Located on the leg, arm and front of the torso; the photo was captured at a distance; male contributor, age 18–29 — 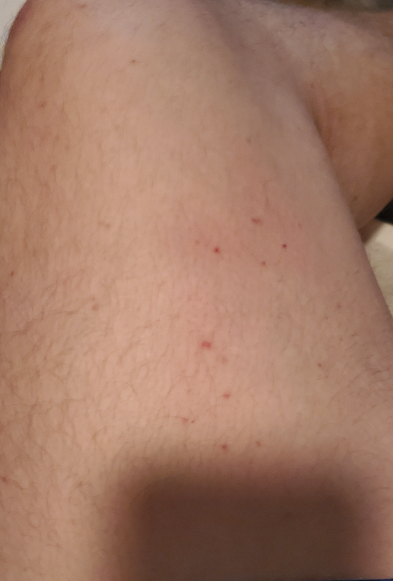Notes:
- assessment — ungradable on photographic review
- reported symptoms — enlargement and itching
- patient's own categorization — a rash
- lesion texture — raised or bumpy